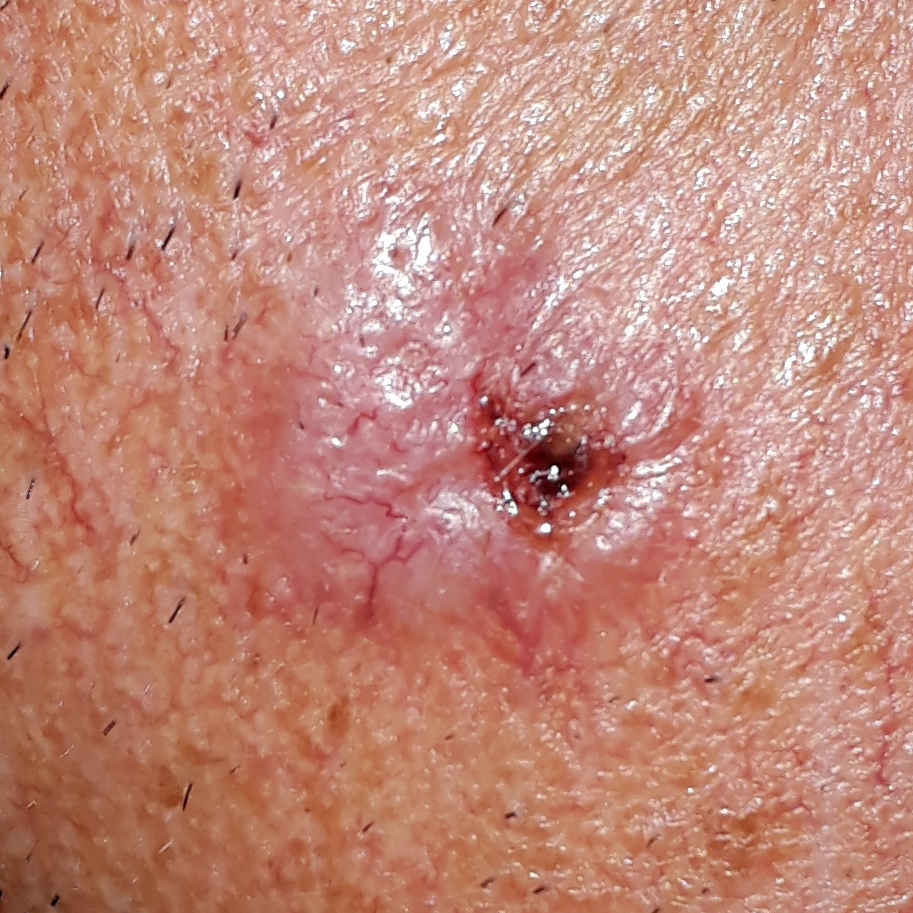Summary: A male subject aged 48. A clinical photo of a skin lesion taken with a smartphone. Skin type II. The chart records prior skin cancer (patient or family) and pesticide exposure. The lesion measures approximately 15 × 14 mm. By the patient's account, the lesion itches, is elevated, has grown, and has bled, but has not changed. Pathology: The biopsy diagnosis was a malignant skin lesion — a basal cell carcinoma.